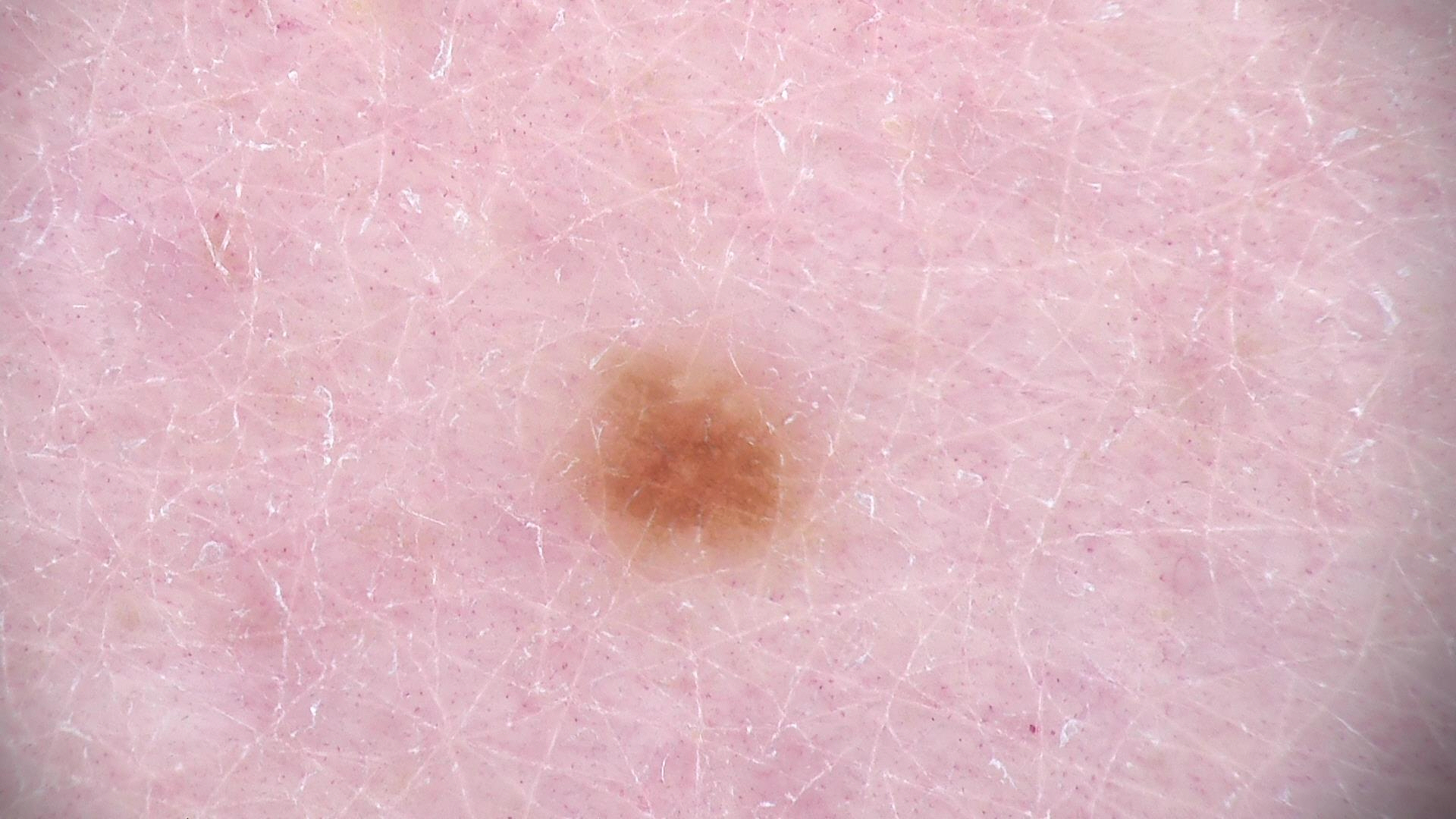Dermoscopy of a skin lesion.
The architecture is that of a banal lesion.
The diagnostic label was a junctional nevus.